A dermoscopic photograph of a skin lesion:
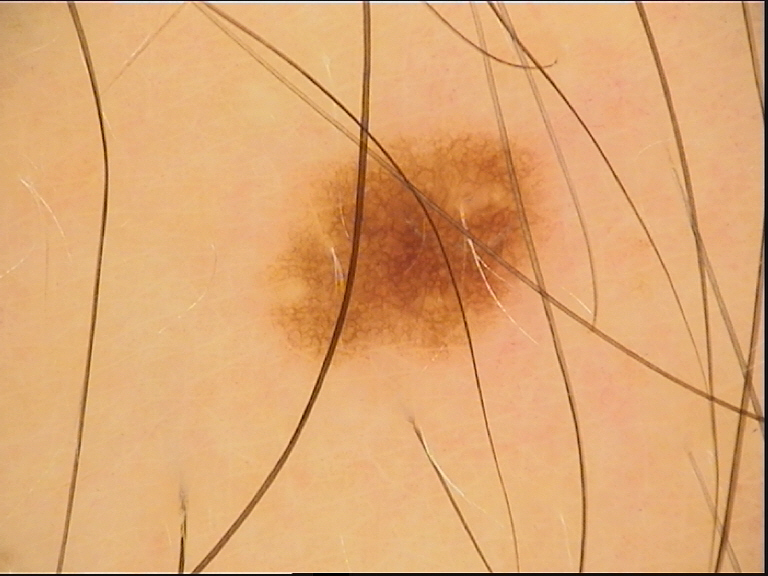Impression: Consistent with a banal lesion — a junctional nevus.